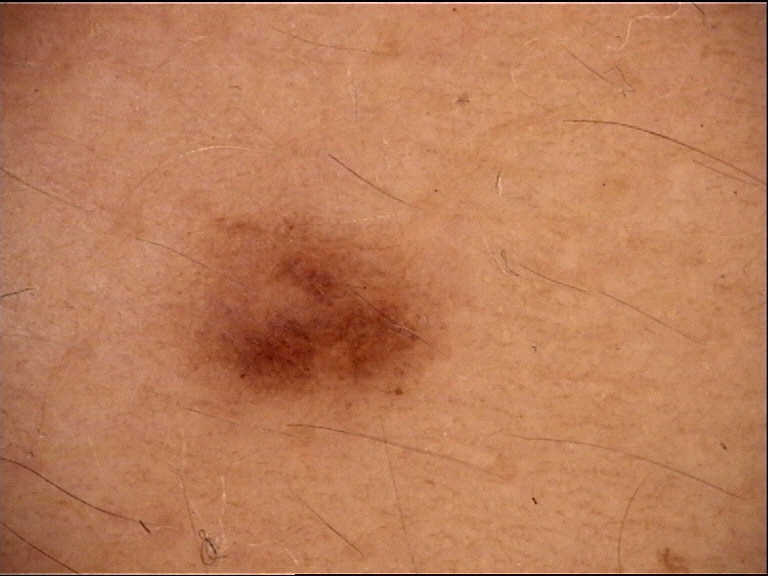Findings:
– imaging · dermoscopy
– diagnosis · dysplastic junctional nevus (expert consensus)